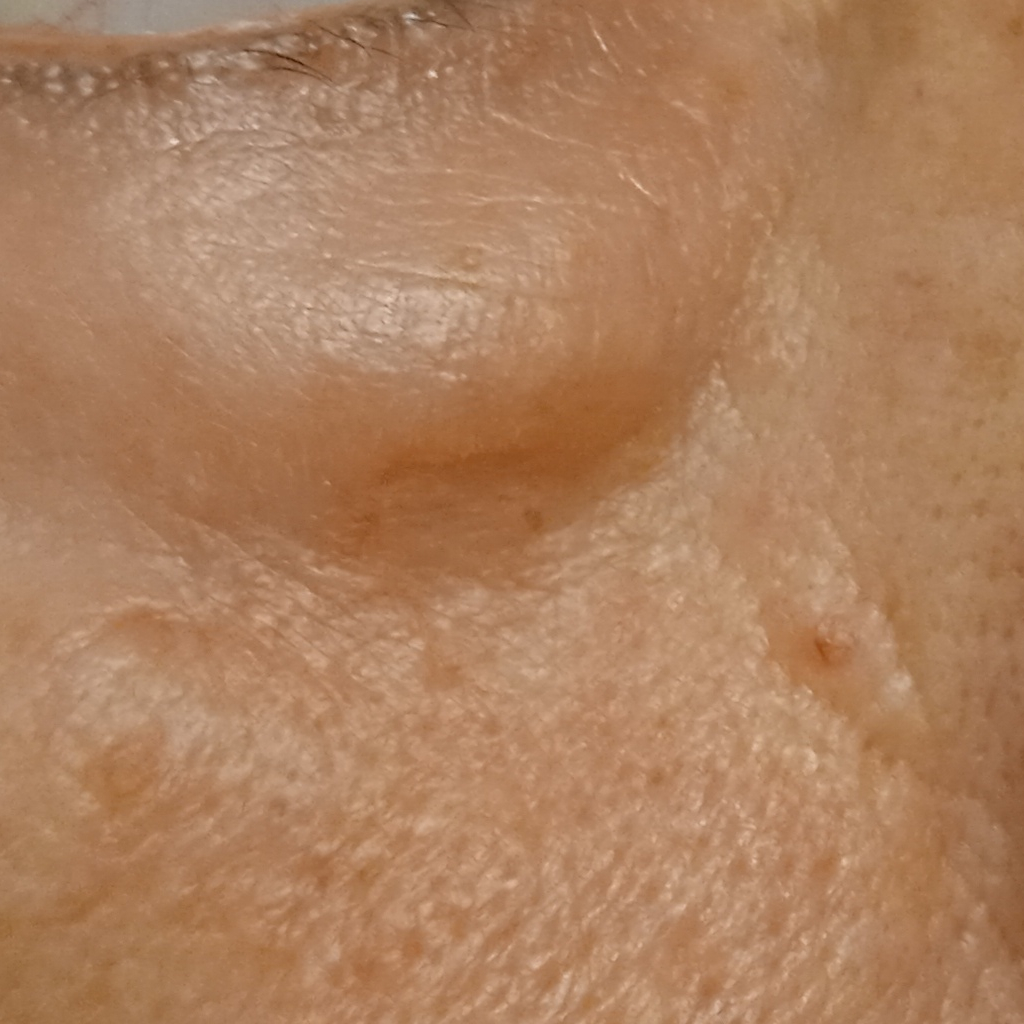- nevus count · few melanocytic nevi overall
- image · clinical photo
- referral context · research study (no referral diagnosis)
- patient · female, age 68
- sun reaction · skin tans without first burning
- site · the face
- diameter · 8.2 mm
- diagnostic label · basal cell carcinoma (dermatologist consensus)